No associated systemic symptoms reported; the patient described the issue as a rash; the patient is a male aged 50–59; symptoms reported: itching; the lesion is described as raised or bumpy; the lesion involves the head or neck; the photo was captured at an angle — 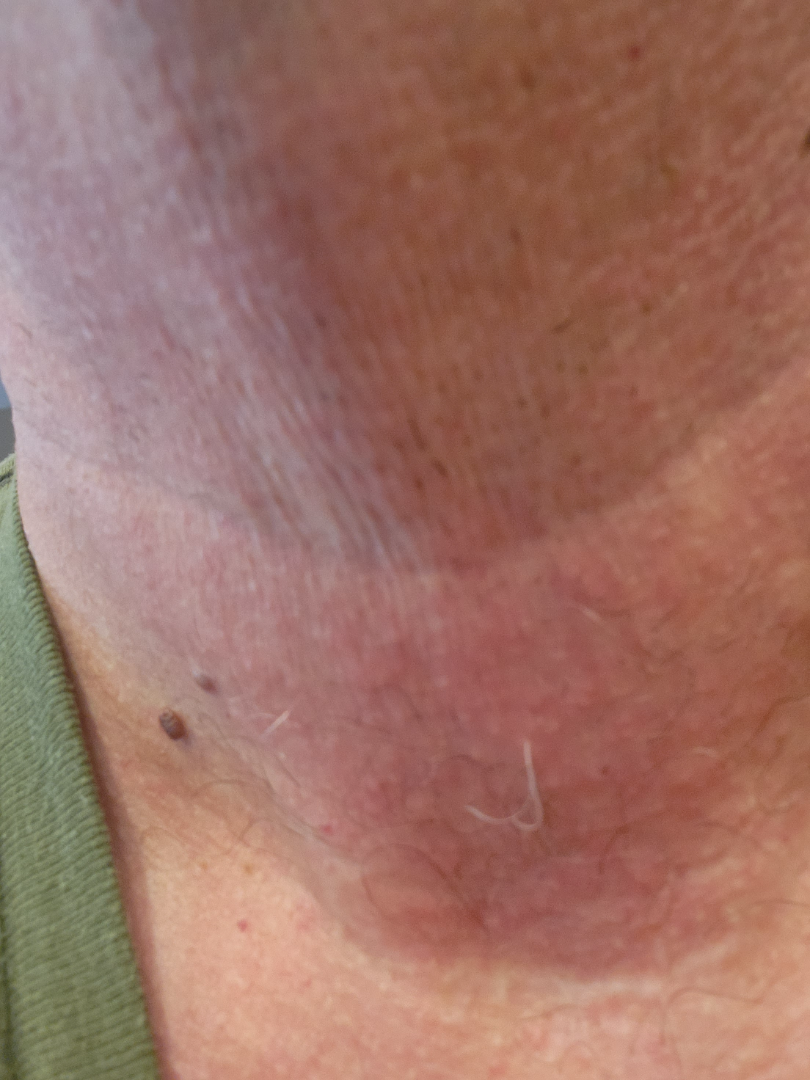The case was indeterminate on photographic review.